A dermatoscopic image of a skin lesion. A male subject, aged approximately 30:
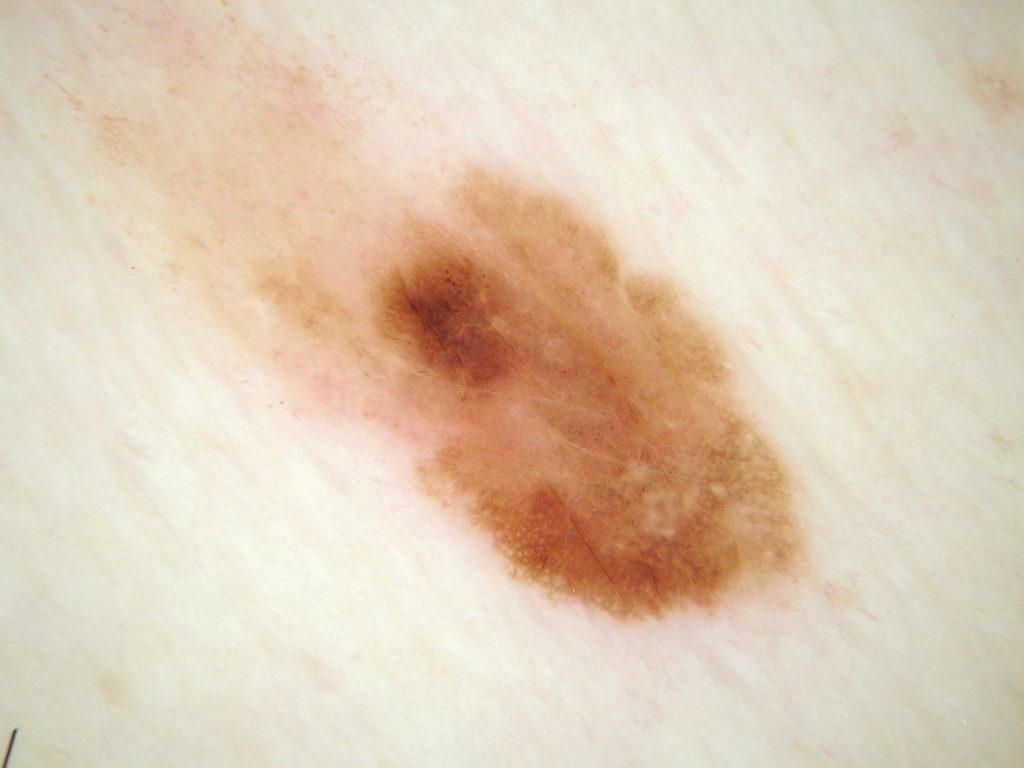Findings:
* lesion bbox — [27,5,820,642]
* features — pigment network
* impression — a melanocytic nevus, a benign skin lesion